The contributor notes the lesion is raised or bumpy · the affected area is the leg · present for less than one week · the contributor notes itching · male patient, age 40–49 · the photograph is a close-up of the affected area · the patient described the issue as a rash: 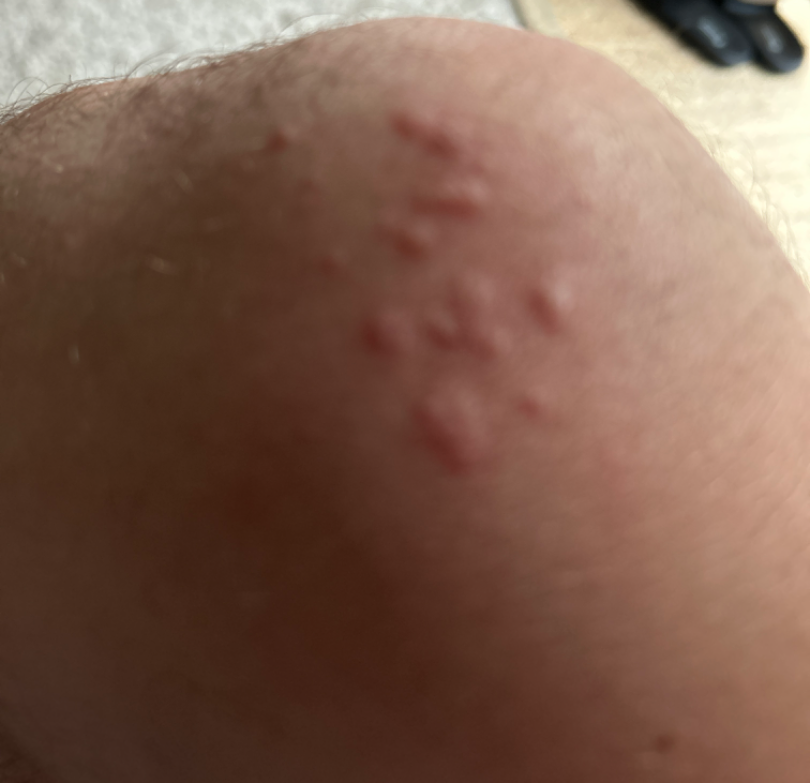The case was indeterminate on photographic review.